A contact-polarized dermoscopy image of a skin lesion. A male patient aged approximately 60 — 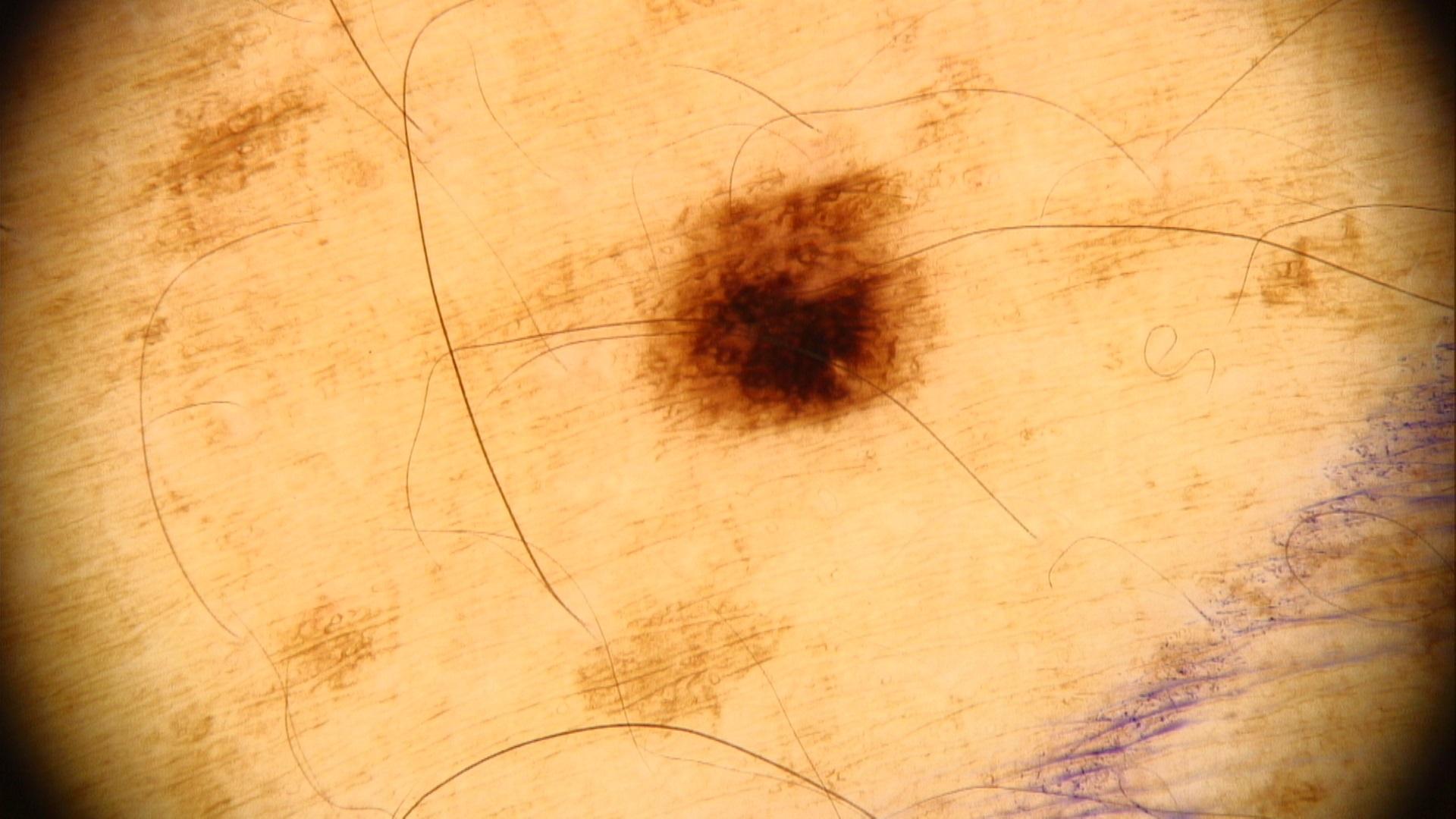diagnosis:
  name: Nevus
  malignancy: benign
  confirmation: expert clinical impression
  lineage: melanocytic